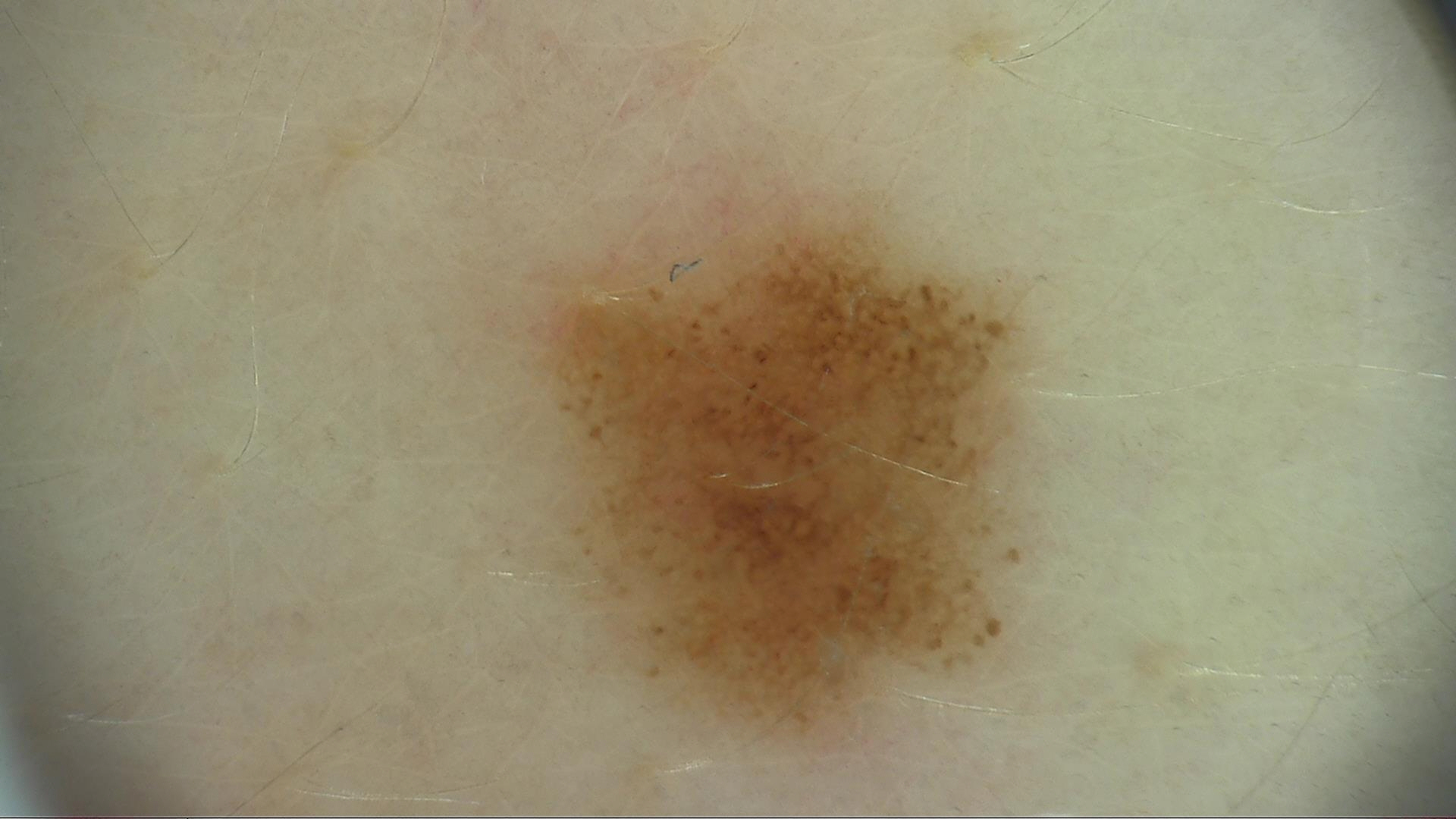Labeled as a dysplastic junctional nevus.